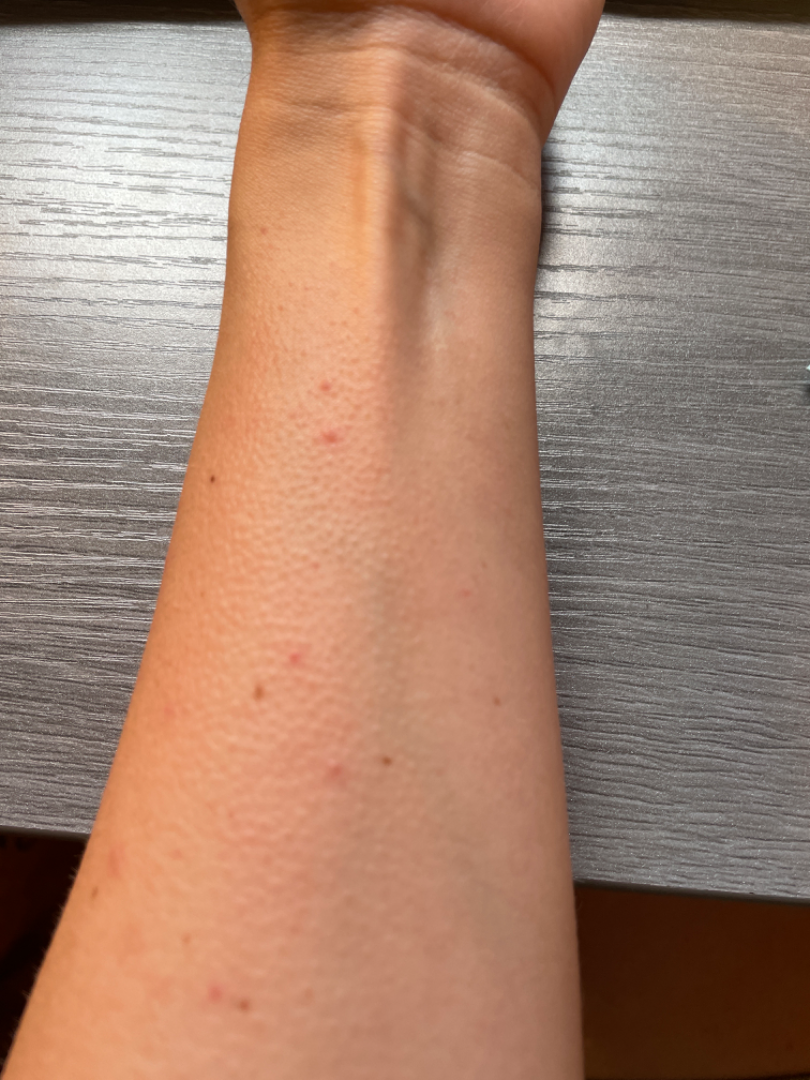The condition could not be reliably identified from the image. Located on the arm. Reported lesion symptoms include itching. The patient reported no systemic symptoms. The lesion is described as raised or bumpy. The patient is 30–39, female. Present for less than one week. Close-up view. The patient described the issue as a rash.